This image was taken at an angle: 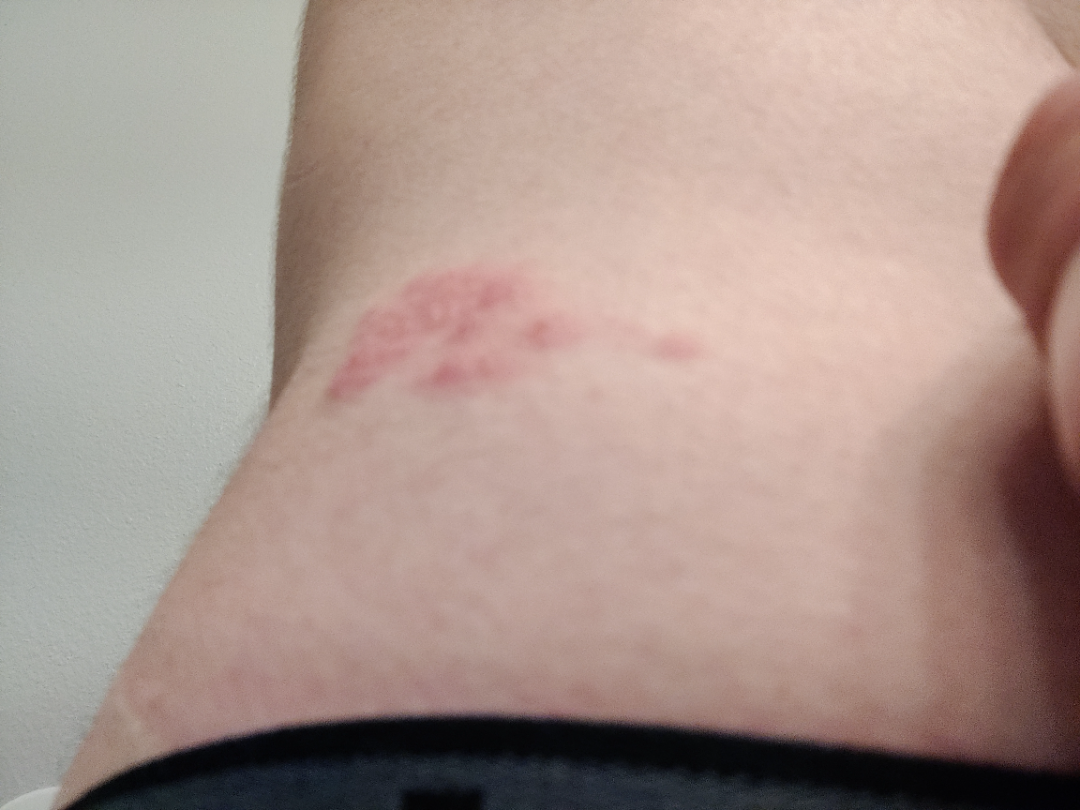On photographic review by a dermatologist, Herpes Zoster (leading).